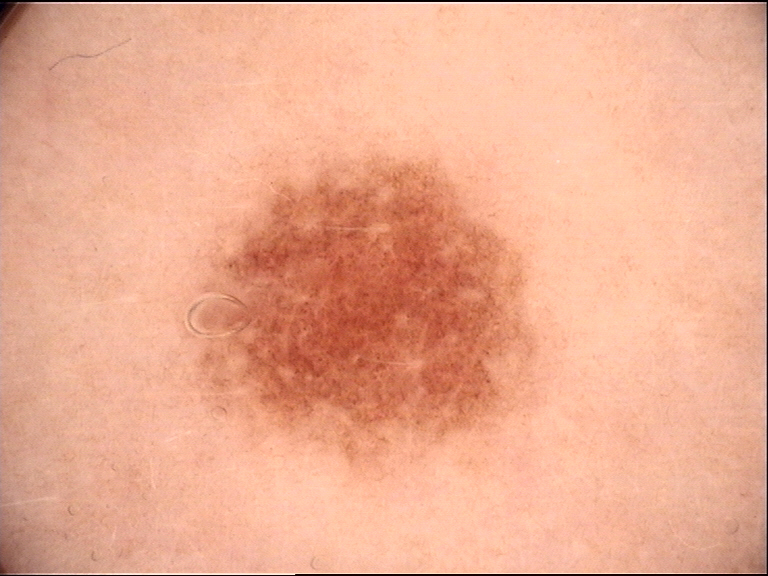- imaging — dermatoscopy
- label — dysplastic junctional nevus (expert consensus)